A dermoscopic photograph of a skin lesion.
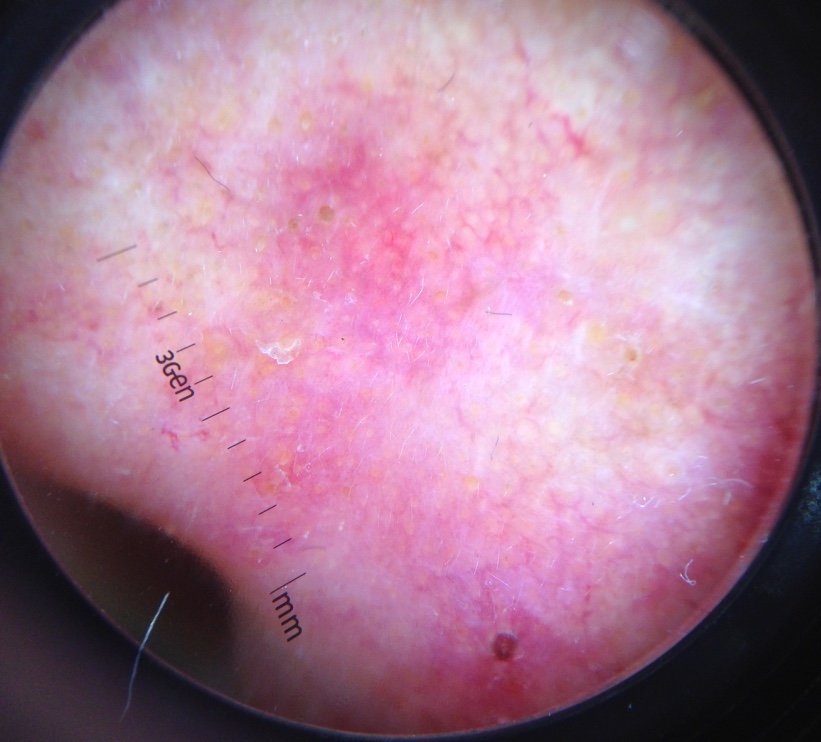Diagnosed as a keratinocytic, indeterminate lesion — an actinic keratosis.